The contributor is 40–49, female; located on the front of the torso; the photo was captured at a distance:
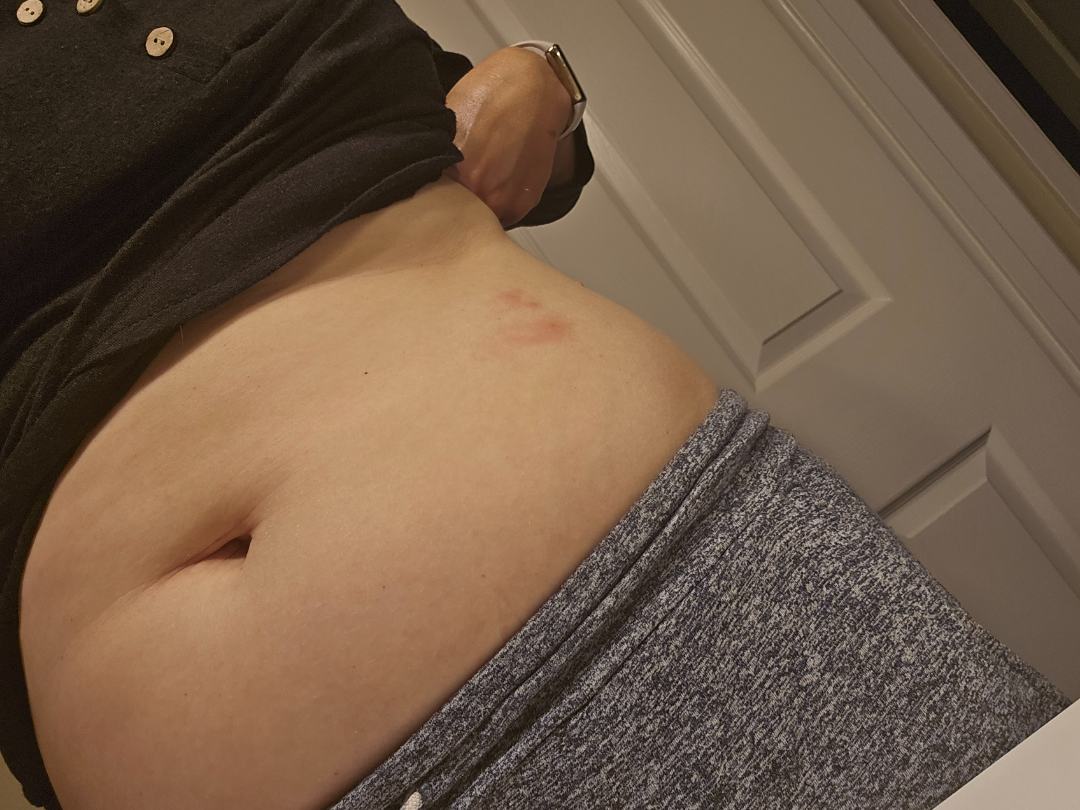  assessment: indeterminate from the photograph